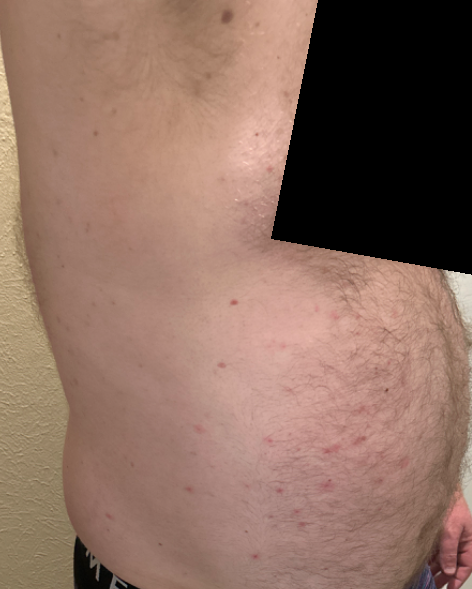Findings:
- assessment · could not be assessed
- photo taken · at a distance